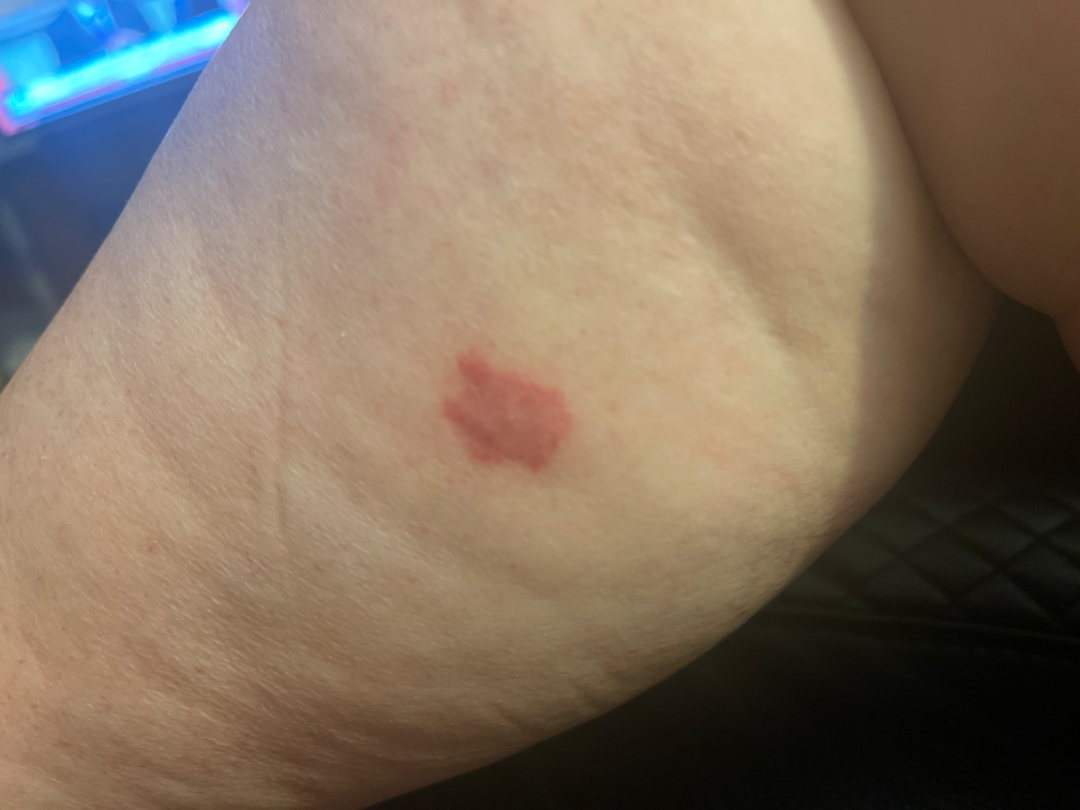texture:
  - flat
  - raised or bumpy
systemic_symptoms: none reported
symptoms:
  - itching
  - darkening
  - bothersome appearance
duration: less than one week
shot_type: close-up
body_site: leg
skin_tone:
  fitzpatrick: I
  monk_skin_tone:
    - 2
    - 3
differential:
  leading:
    - Hemangioma
  considered:
    - Insect Bite
    - Tufted angioma of skin